Dermoscopy of a skin lesion: 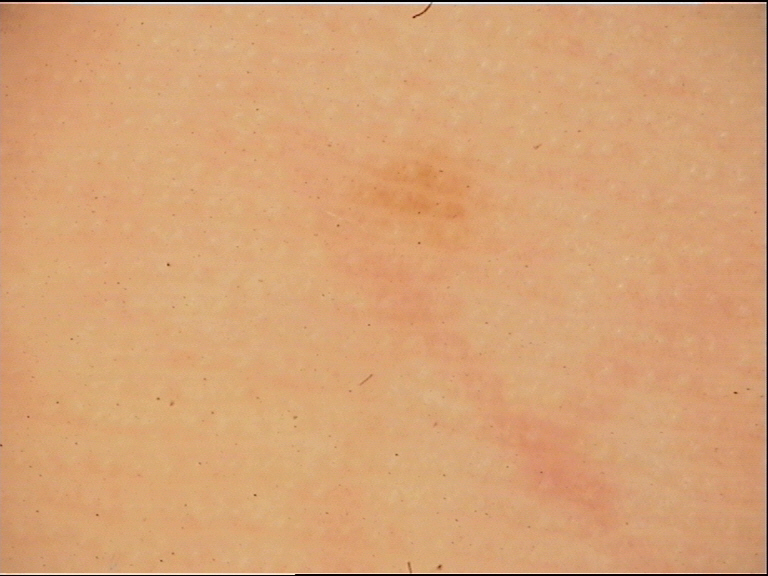| field | value |
|---|---|
| category | banal |
| label | acral junctional nevus (expert consensus) |